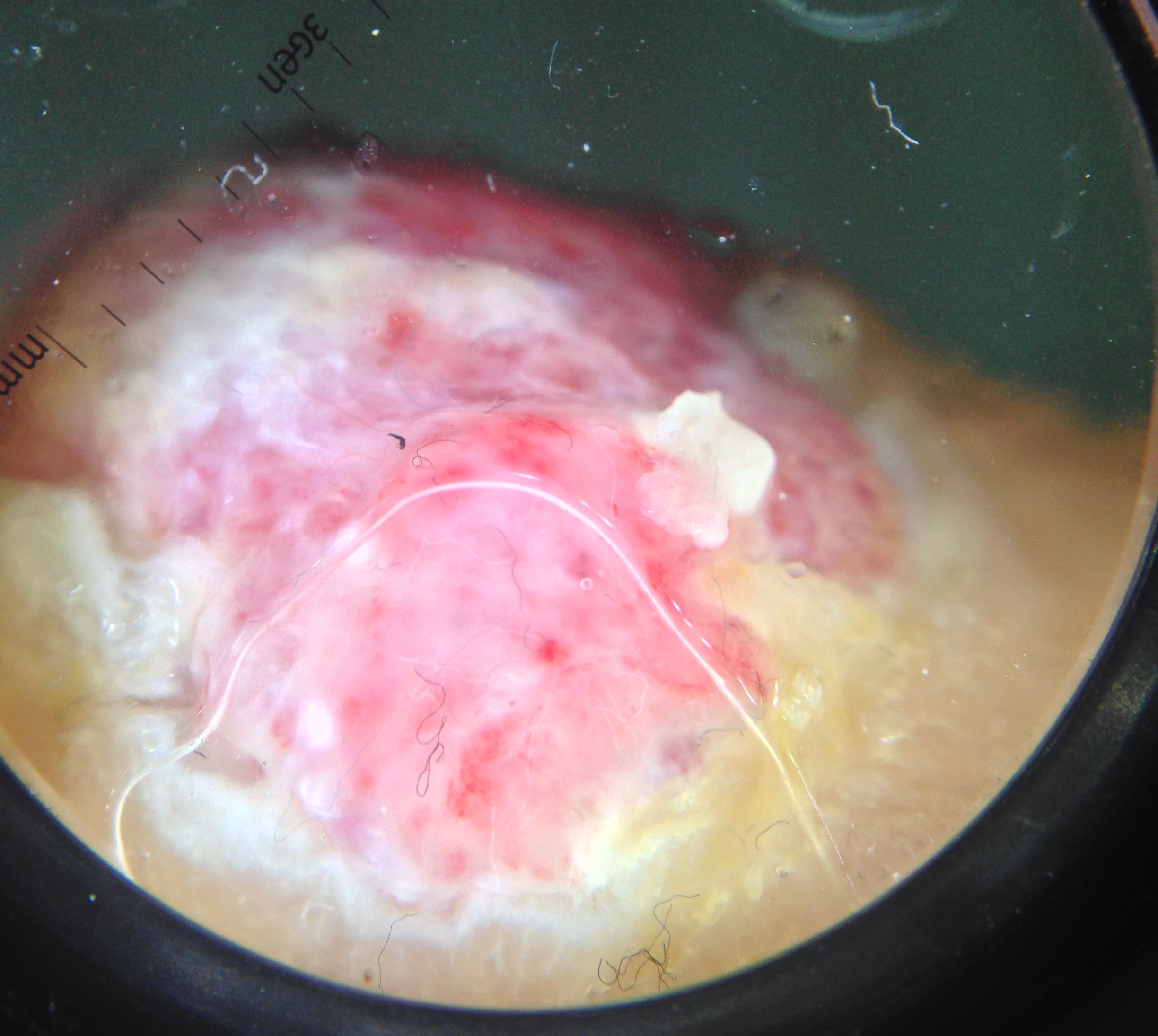A dermoscopic close-up of a skin lesion. Confirmed on histopathology as an acral nodular melanoma.